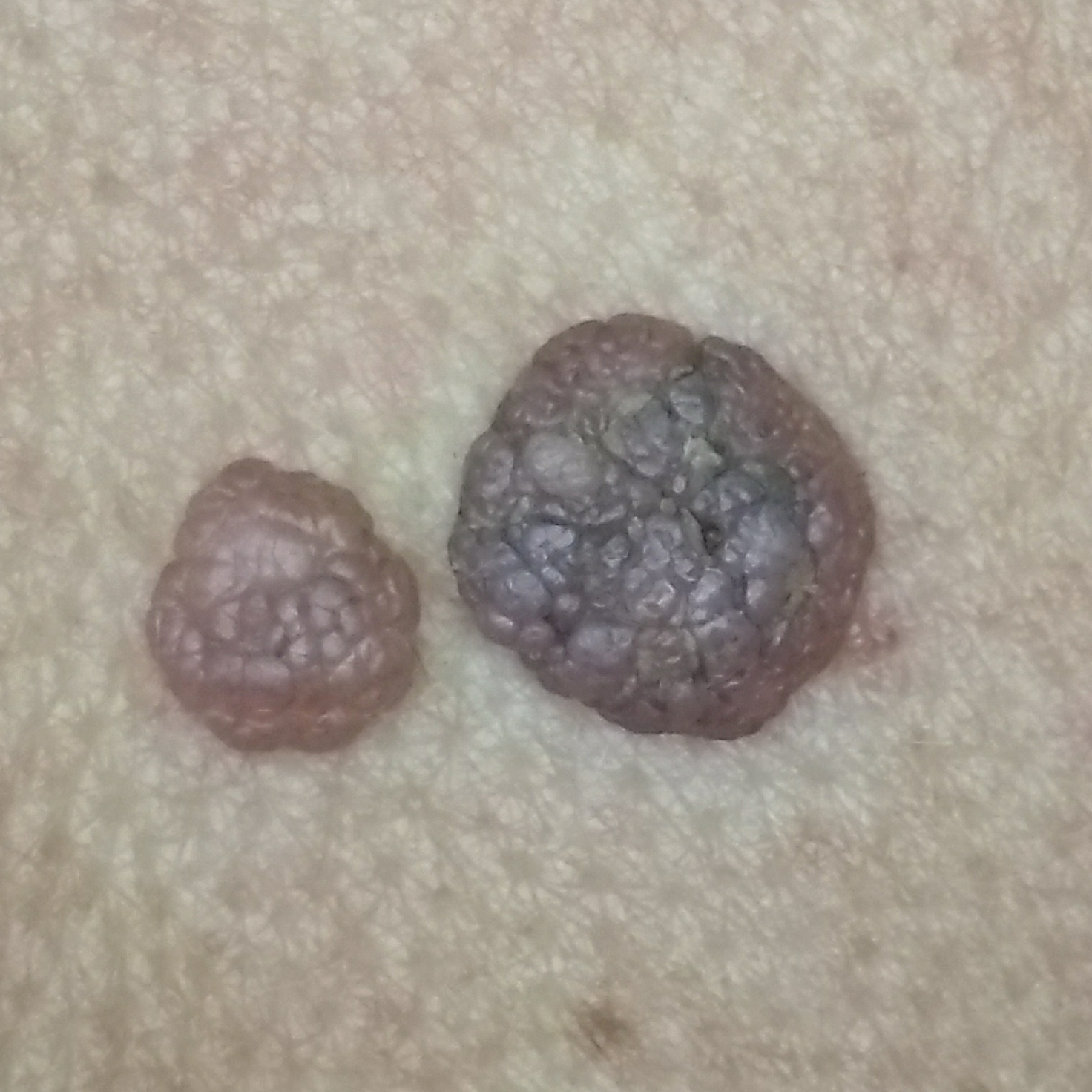<lesion>
  <patient>
    <age>38</age>
  </patient>
  <symptoms>
    <present>growth, elevation</present>
    <absent>itching</absent>
  </symptoms>
  <diagnosis>
    <name>nevus</name>
    <code>NEV</code>
    <malignancy>benign</malignancy>
    <confirmation>clinical consensus</confirmation>
  </diagnosis>
</lesion>